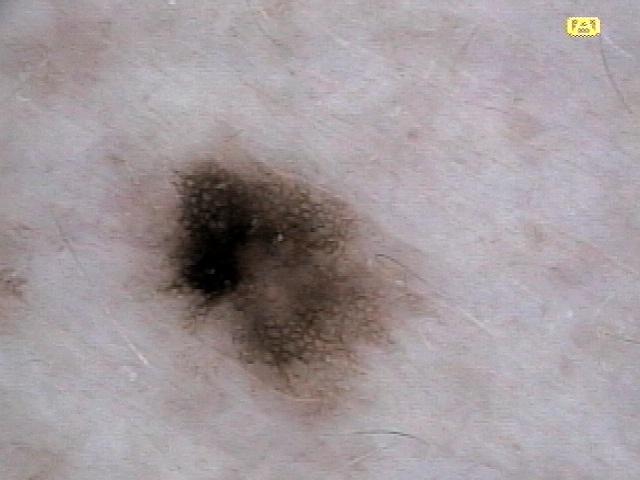diagnostic label=Nevus (biopsy-proven).